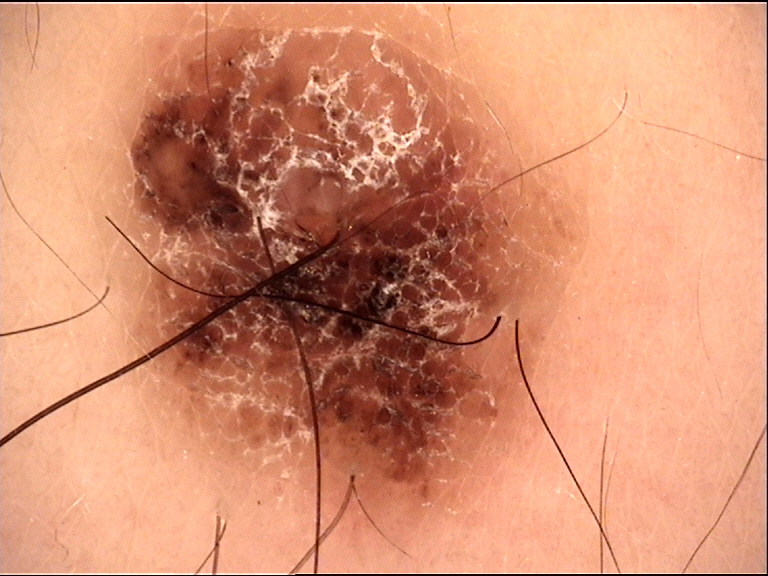Findings:
* label · dysplastic compound nevus (expert consensus)